A female subject 81 years of age. Acquired for a research image collection, with no referral diagnosis. A dermatoscopic image of a skin lesion.
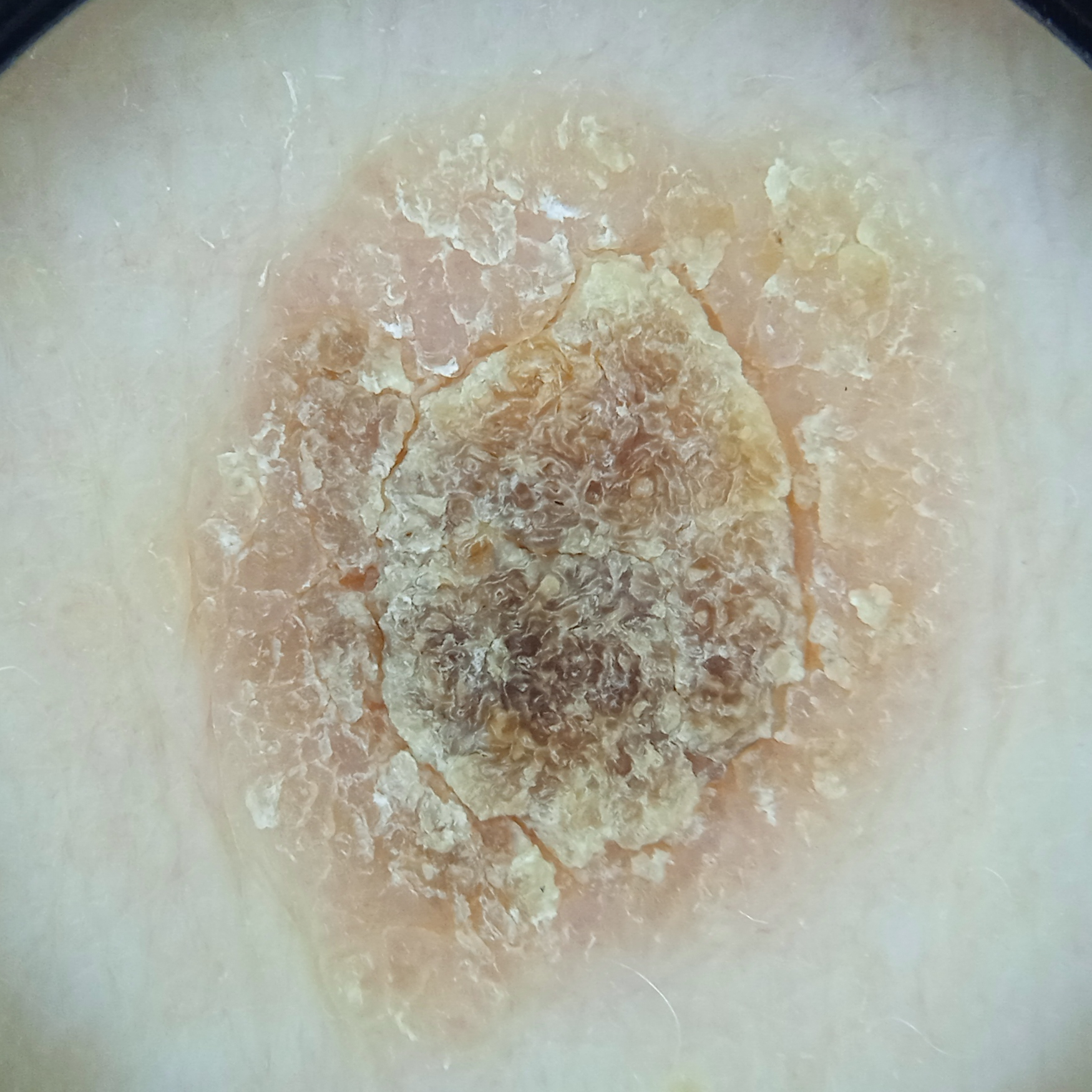The lesion involves the back.
The four-dermatologist consensus diagnosis was a seborrheic keratosis; diagnostic confidence was good.